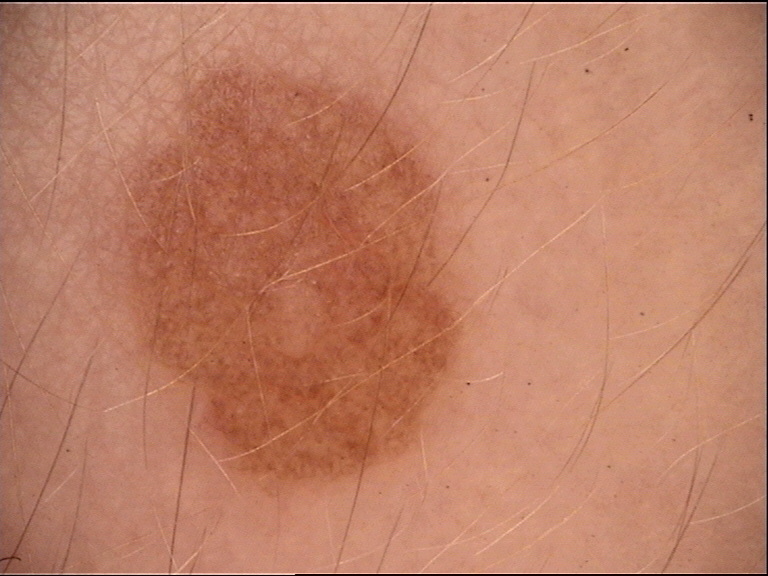Diagnosed as a compound nevus.